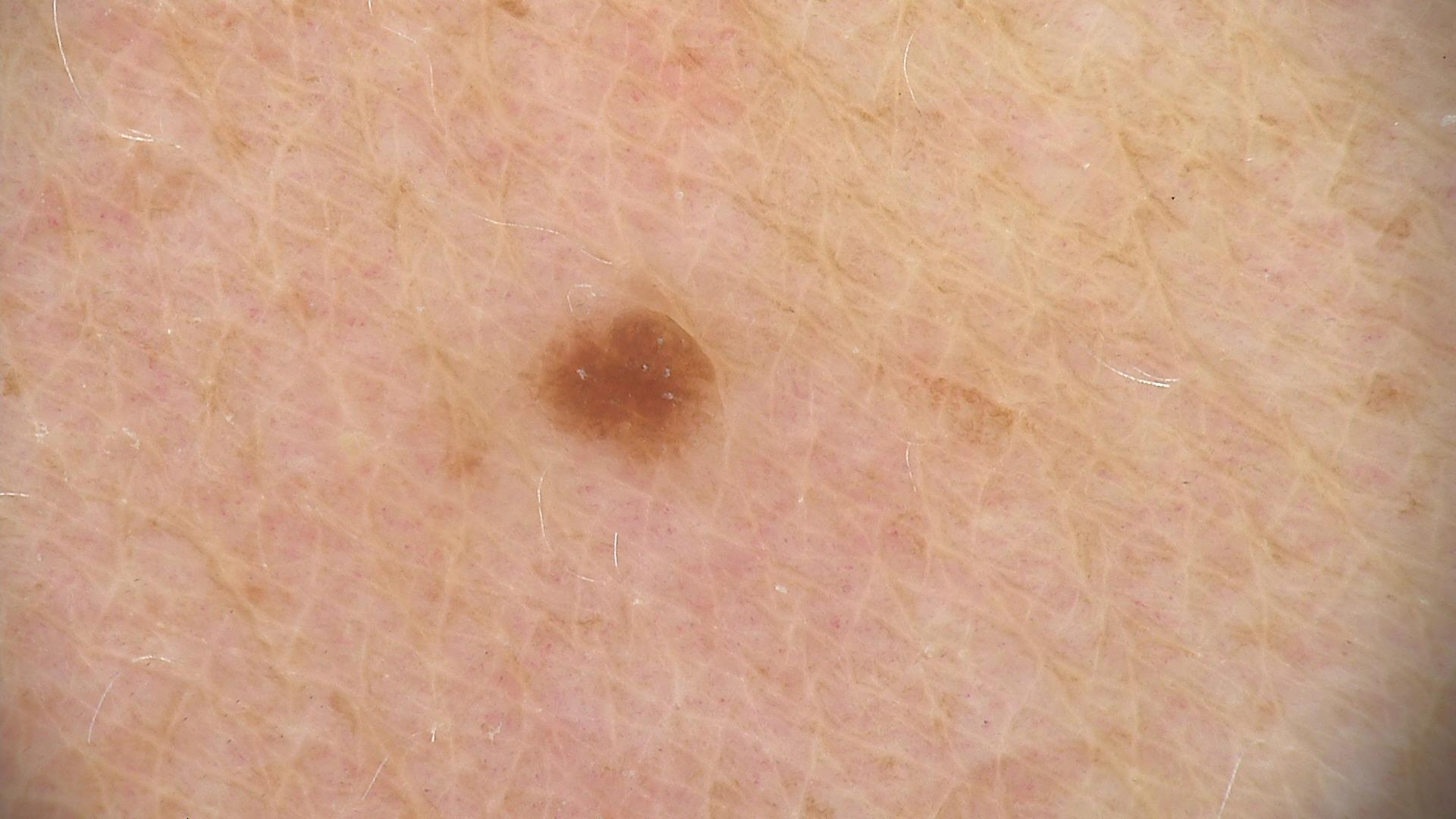{"diagnosis": {"name": "junctional nevus", "code": "jb", "malignancy": "benign", "super_class": "melanocytic", "confirmation": "expert consensus"}}